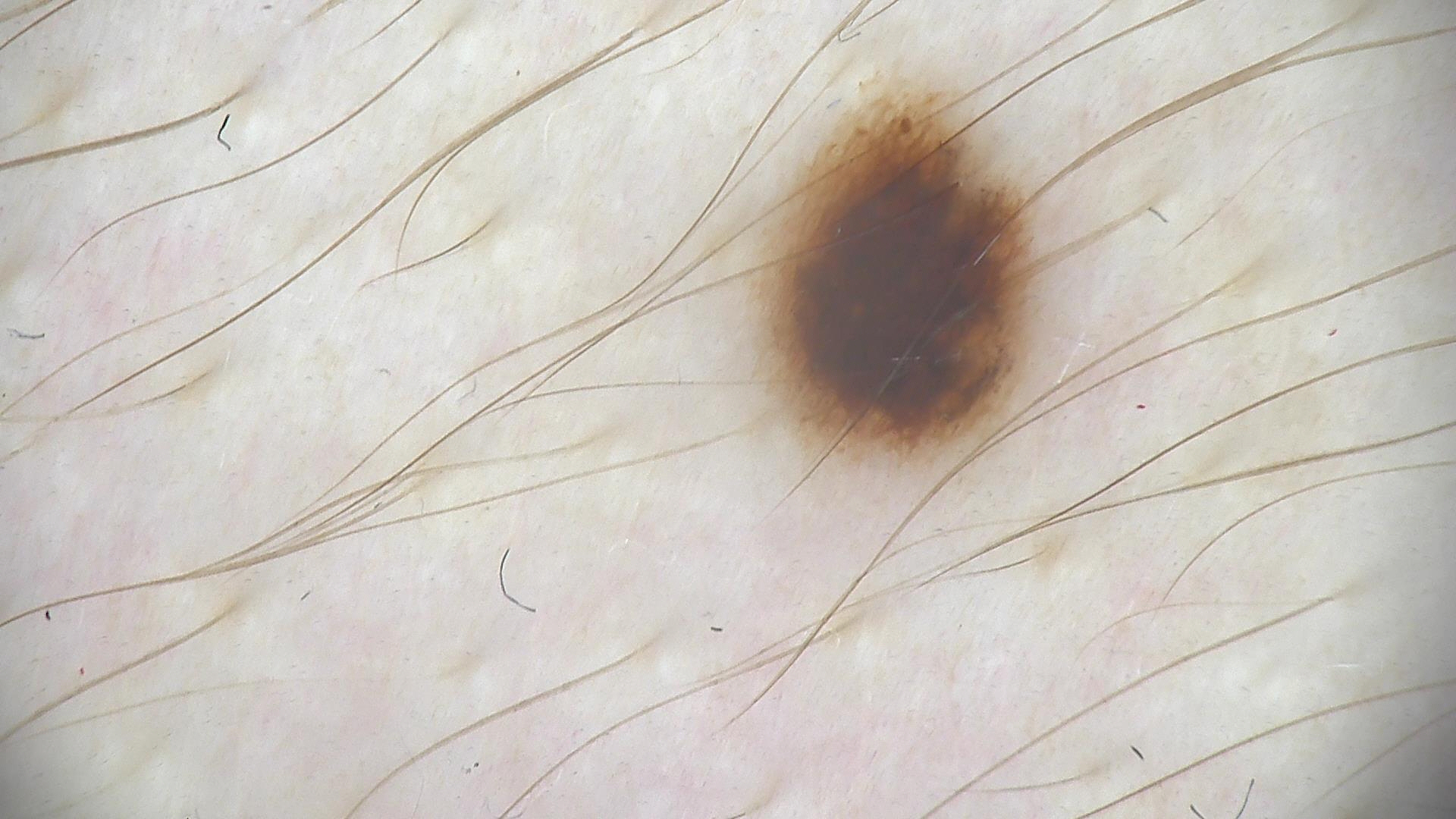| feature | finding |
|---|---|
| diagnosis | dysplastic junctional nevus (expert consensus) |